The patient says their skin reddens with sun exposure.
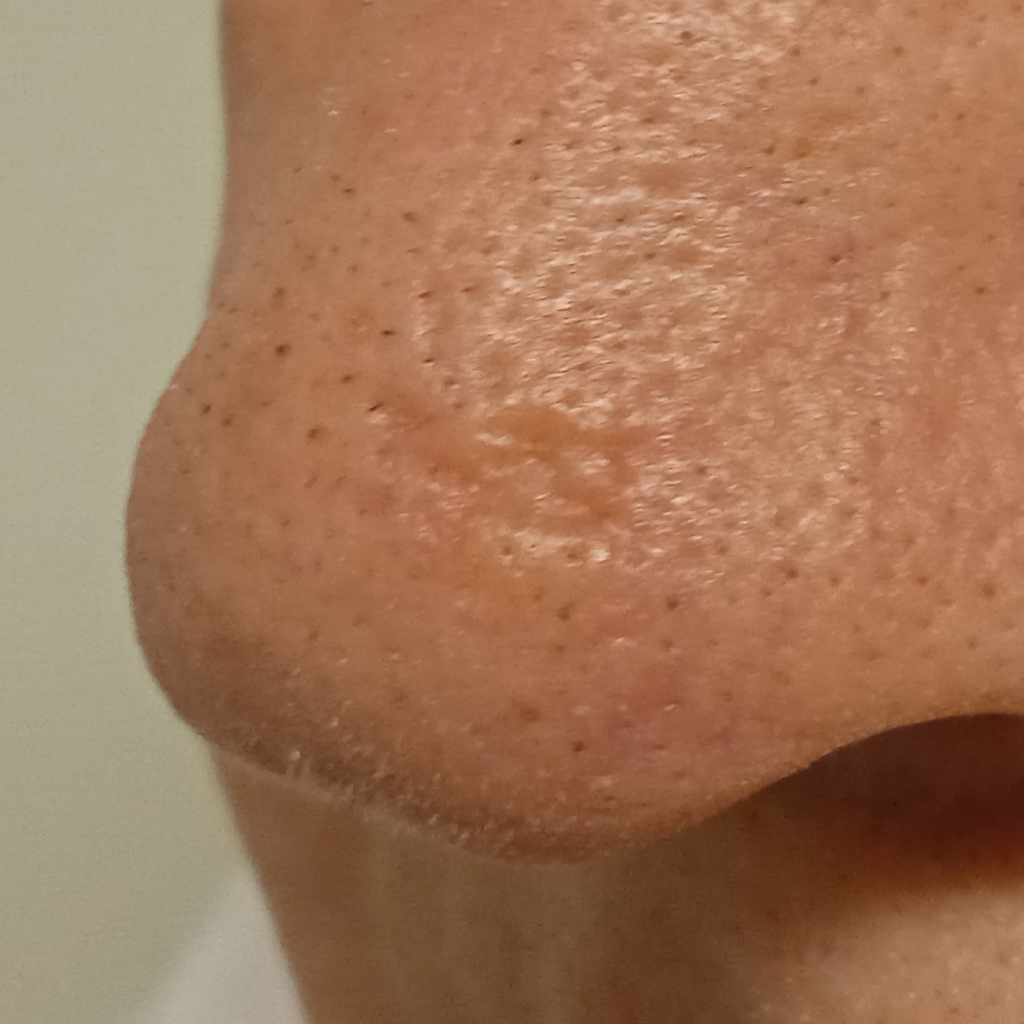lesion size: 8.5 mm; diagnostic label: basal cell carcinoma (biopsy-proven).